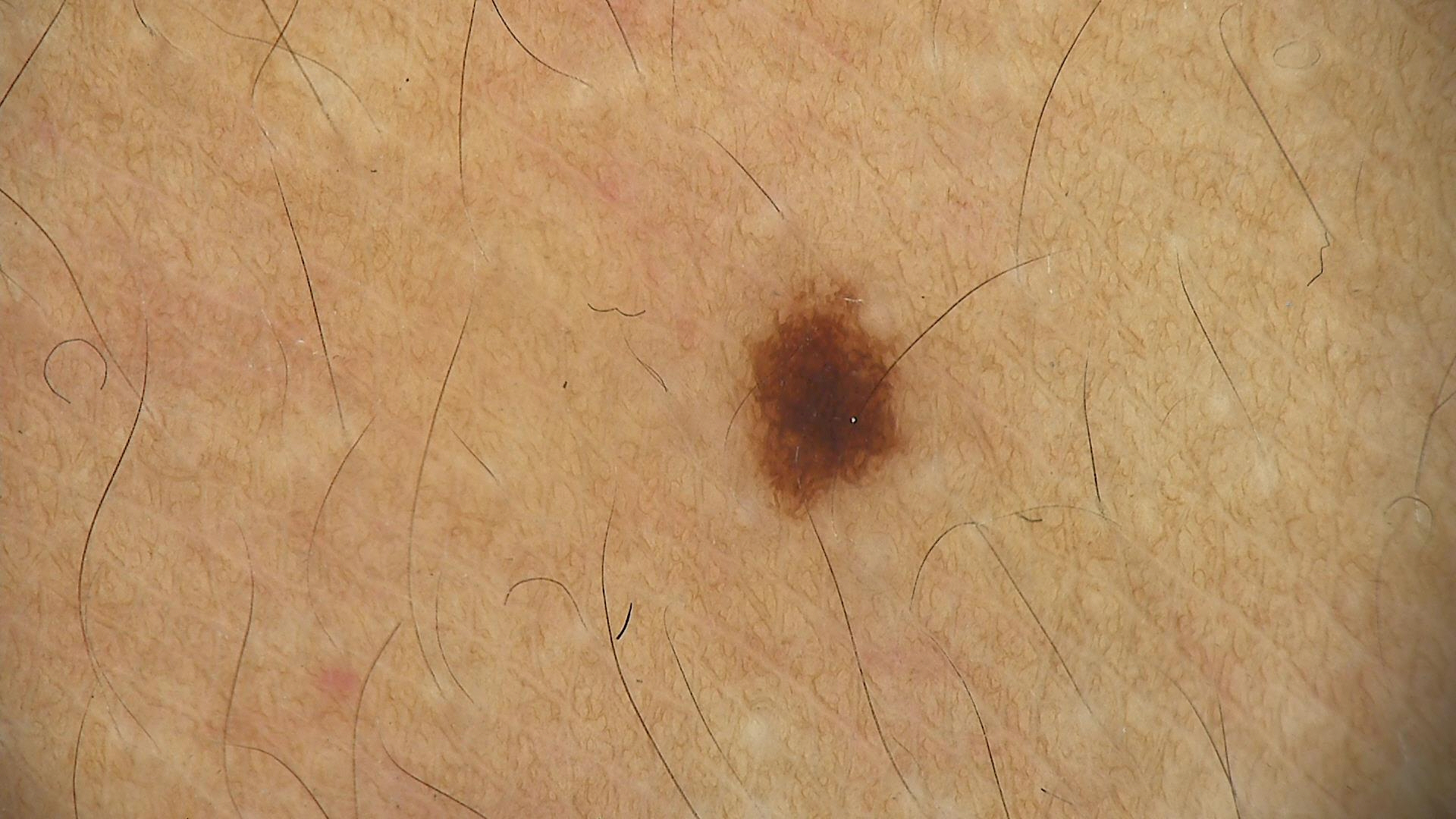Q: What is this lesion?
A: dysplastic junctional nevus (expert consensus)